A skin lesion imaged with a dermatoscope.
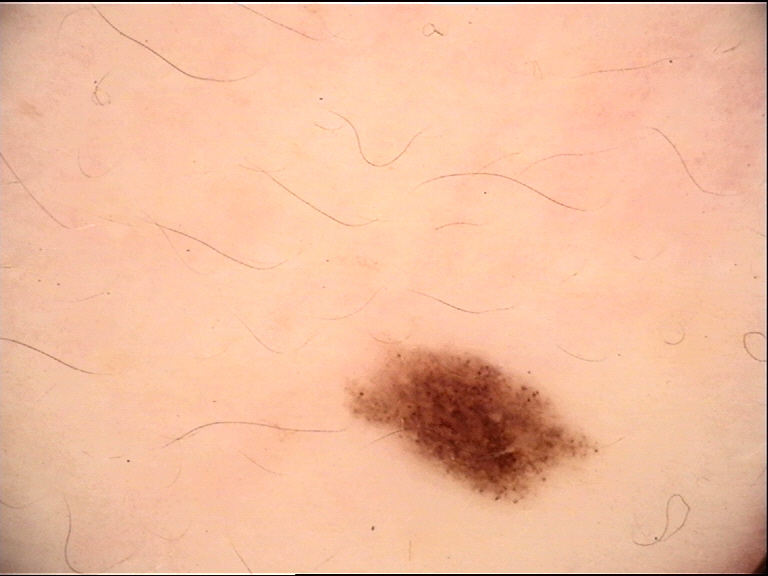{"diagnosis": {"name": "junctional nevus", "code": "jb", "malignancy": "benign", "super_class": "melanocytic", "confirmation": "expert consensus"}}